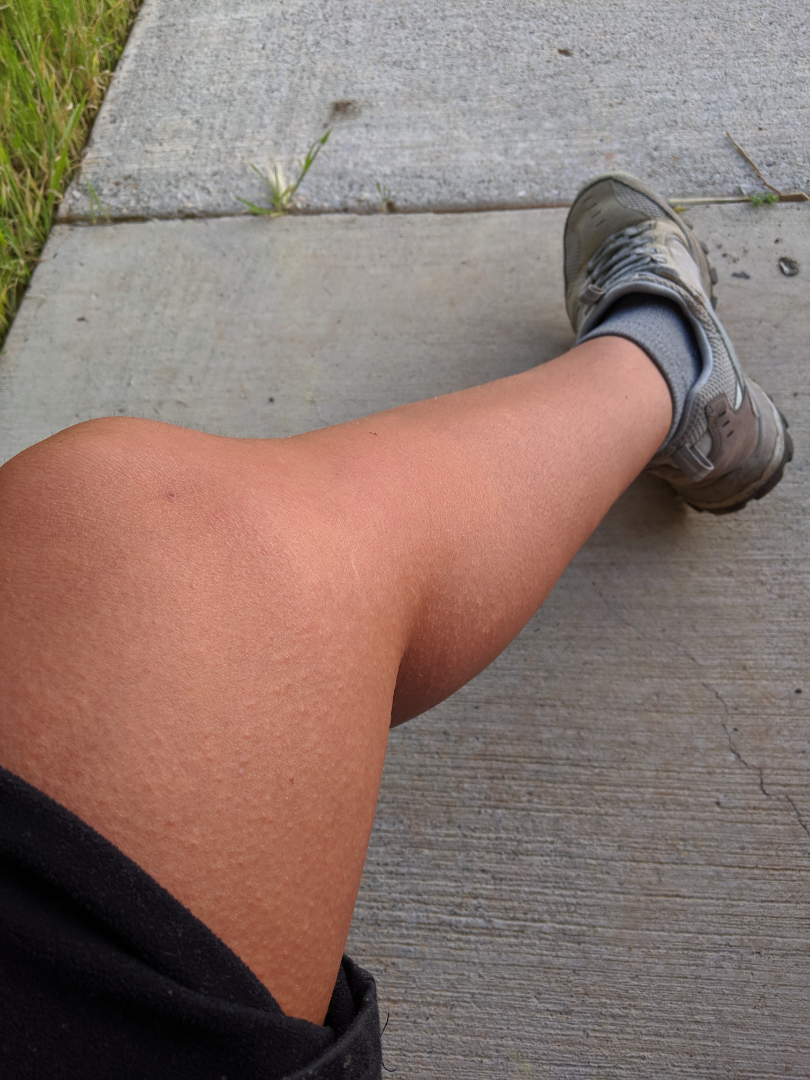assessment=indeterminate; history=about one day; site=leg; image framing=at a distance; symptoms=itching; patient describes the issue as=a rash; described texture=raised or bumpy.